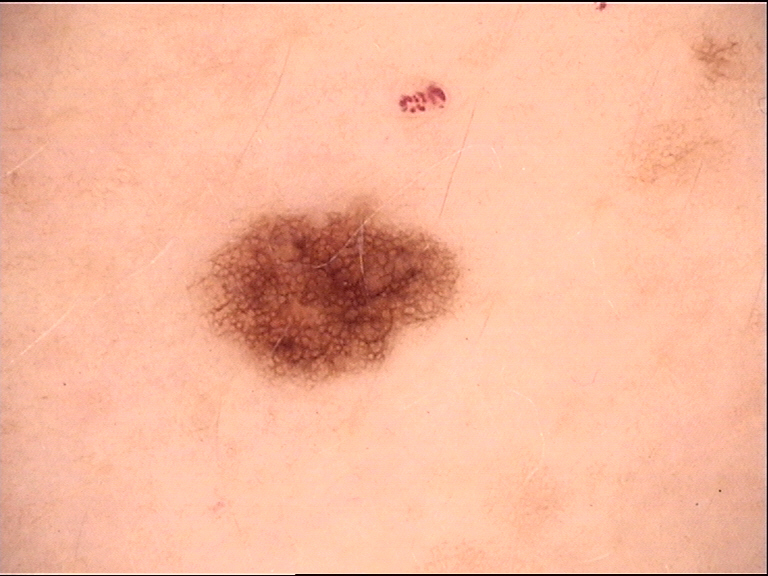class = dysplastic junctional nevus (expert consensus).